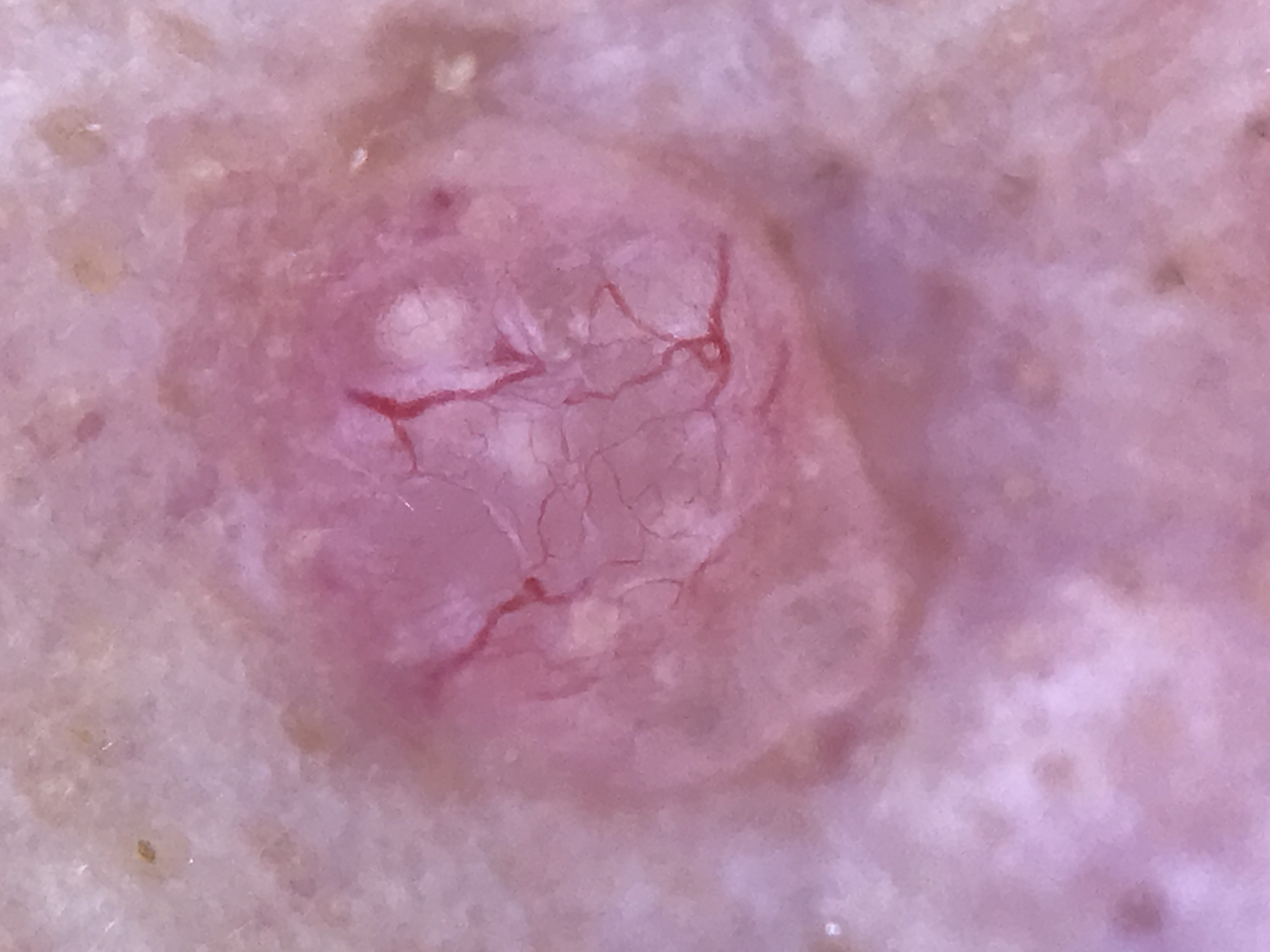Q: What did the workup show?
A: basal cell carcinoma (biopsy-proven)